A skin lesion imaged with a dermatoscope; a male subject aged approximately 40 — 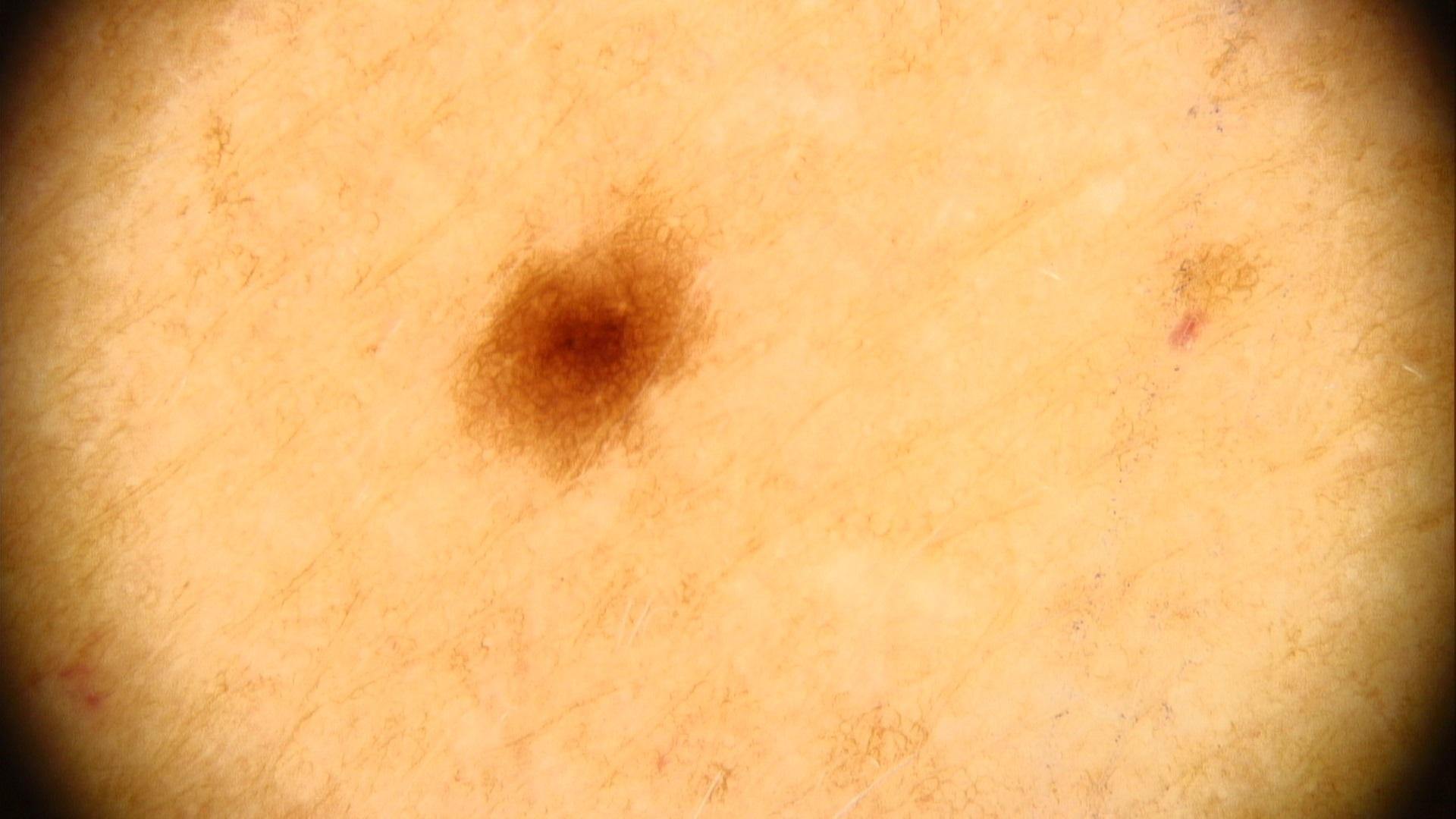lesion_location:
  region: the trunk
  detail: the posterior trunk
diagnosis:
  name: Nevus
  malignancy: benign
  confirmation: expert clinical impression
  lineage: melanocytic